A dermatoscopic image of a skin lesion.
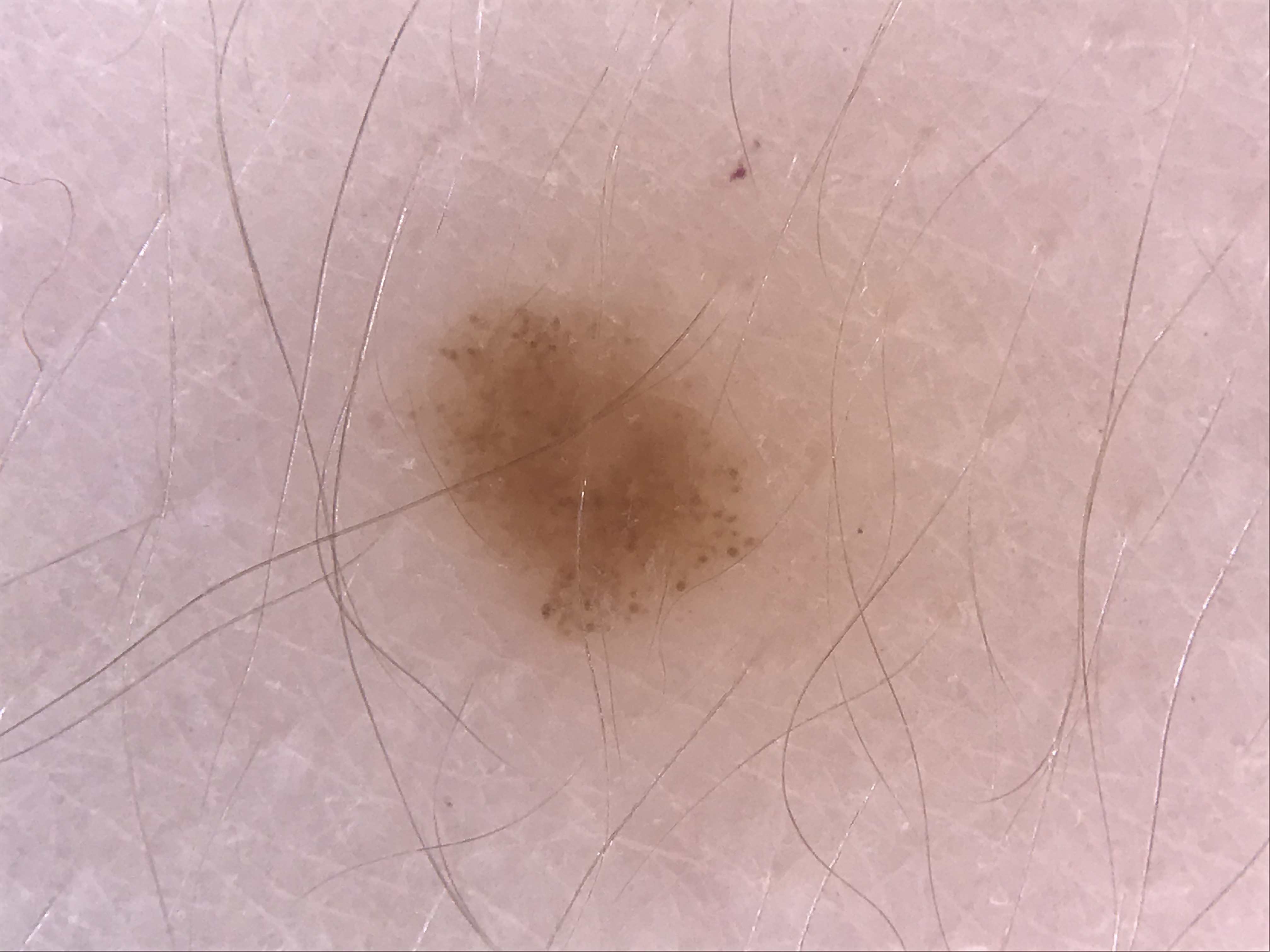Classified as a dysplastic junctional nevus.